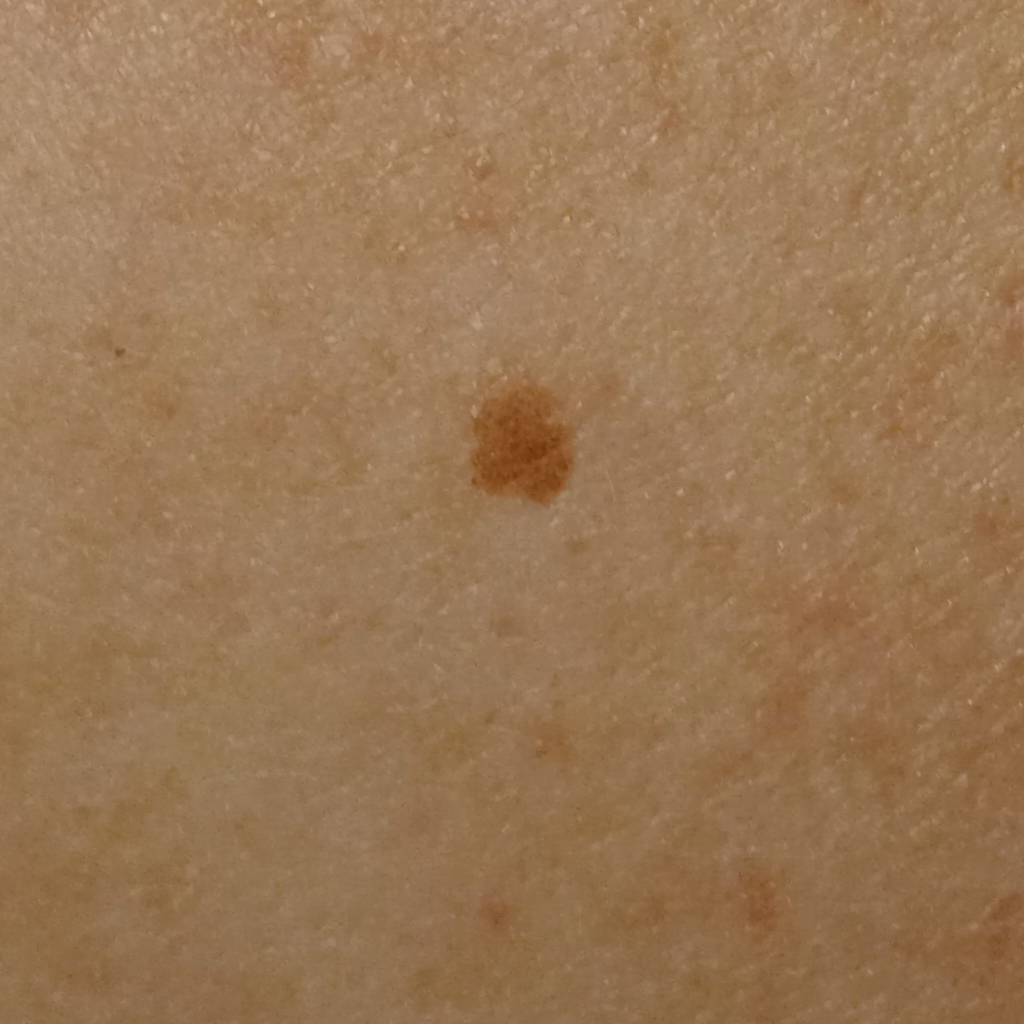Case summary: Imaged for a research study, with no referral diagnosis recorded. A clinical photograph showing a skin lesion. The lesion is on the back. The lesion is about 5.1 mm across. Impression: Dermatologist review favored a melanocytic nevus.